The lesion involves the head or neck. This is a close-up image. The contributor is male — 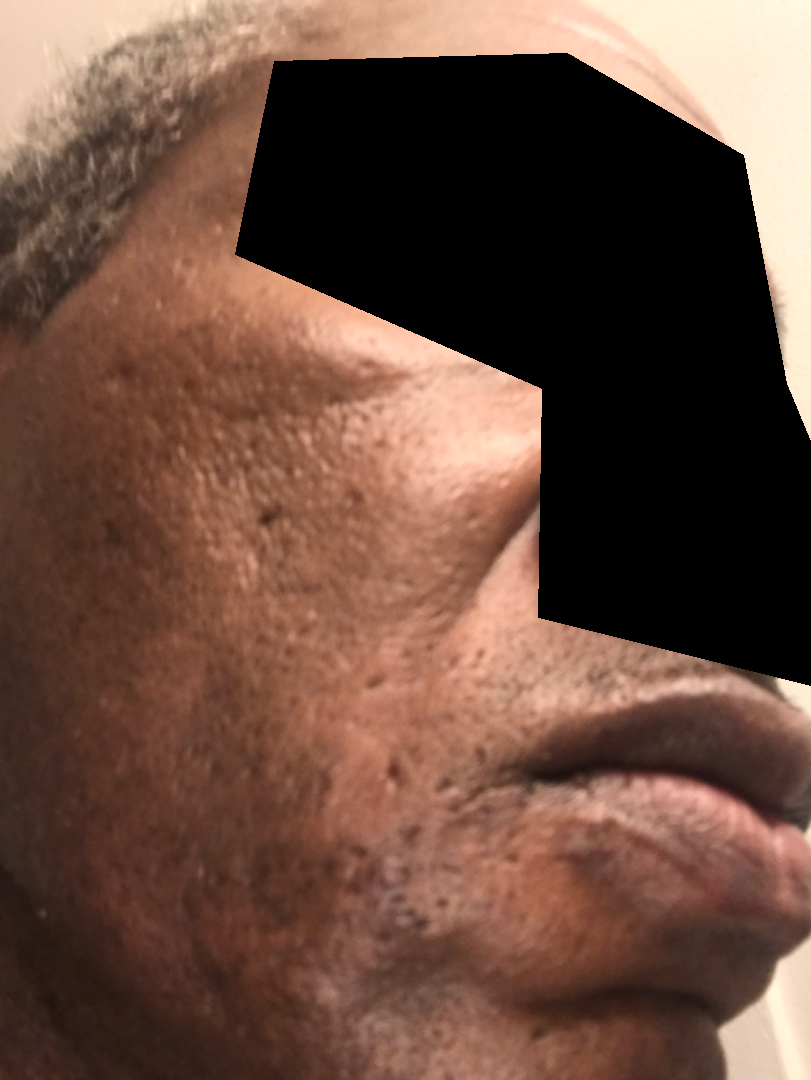Three independent reviewers: the differential, in no particular order, includes Post-Inflammatory hyperpigmentation and Scar Condition.